The patient is Fitzpatrick phototype II. A clinical close-up photograph of a skin lesion. A male subject 72 years old. History notes no pesticide exposure and no prior malignancy (patient or family).
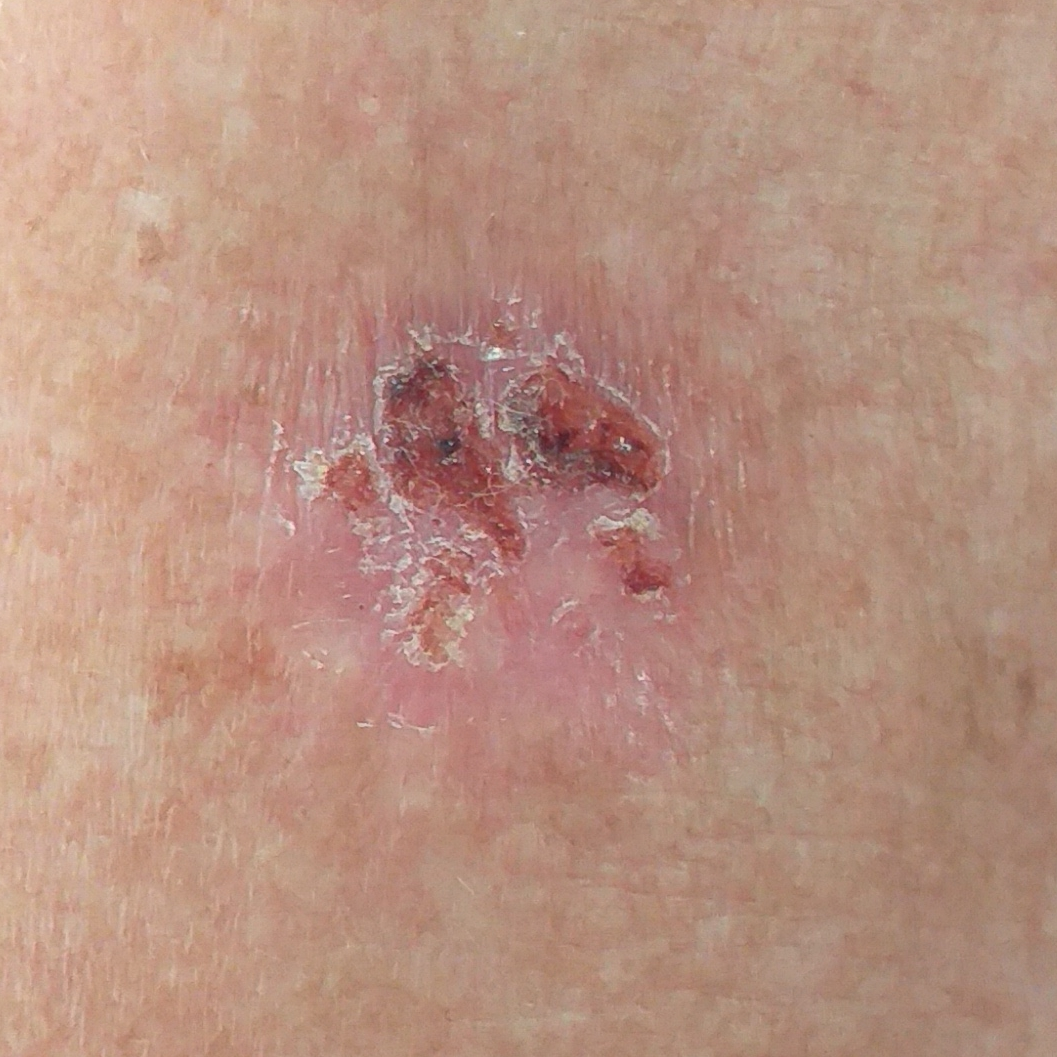| key | value |
|---|---|
| location | the chest |
| lesion size | 15 × 15 mm |
| symptoms | bleeding, elevation, pain, growth, itching |
| diagnosis | basal cell carcinoma (biopsy-proven) |